A dermoscopic image of a skin lesion.
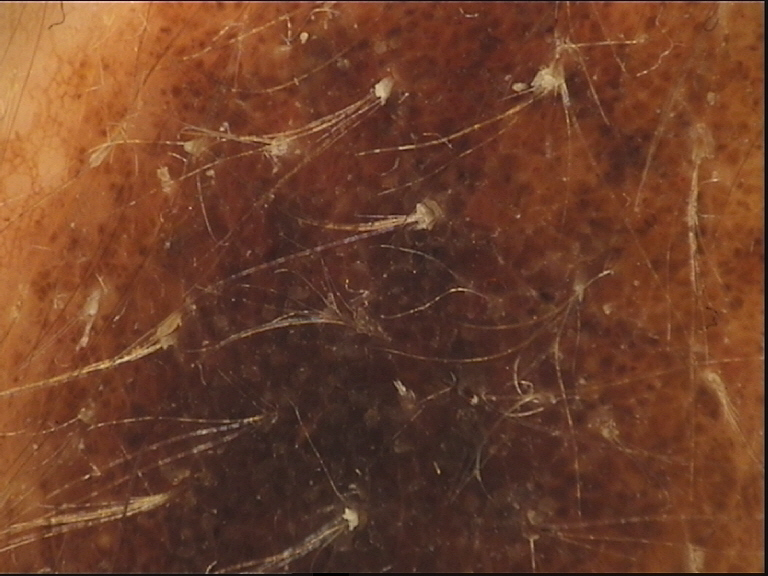This is a banal lesion. Labeled as a congenital compound nevus.